A dermatoscopic image of a skin lesion: 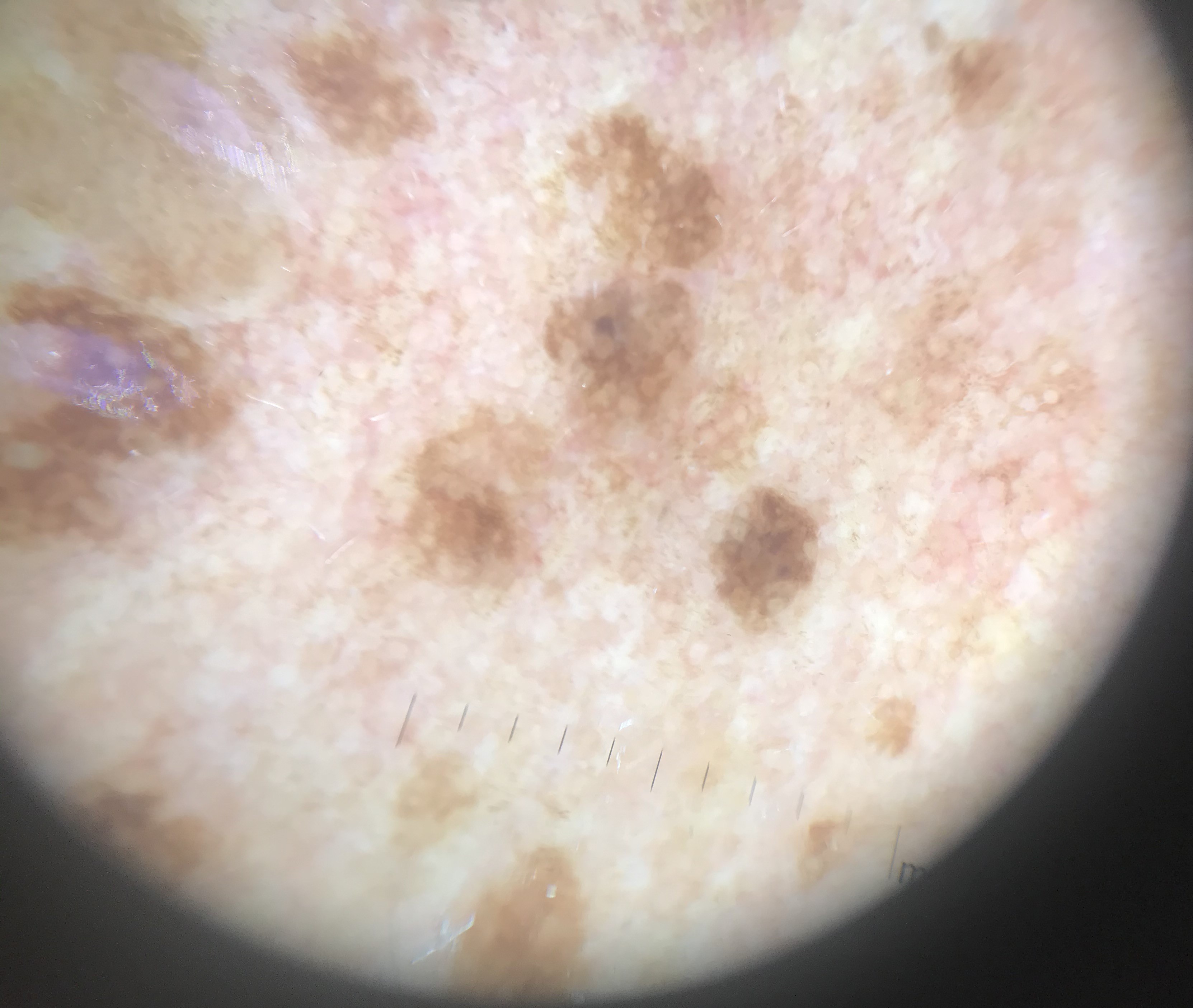The morphology is that of a keratinocytic lesion. The diagnostic label was a seborrheic keratosis.